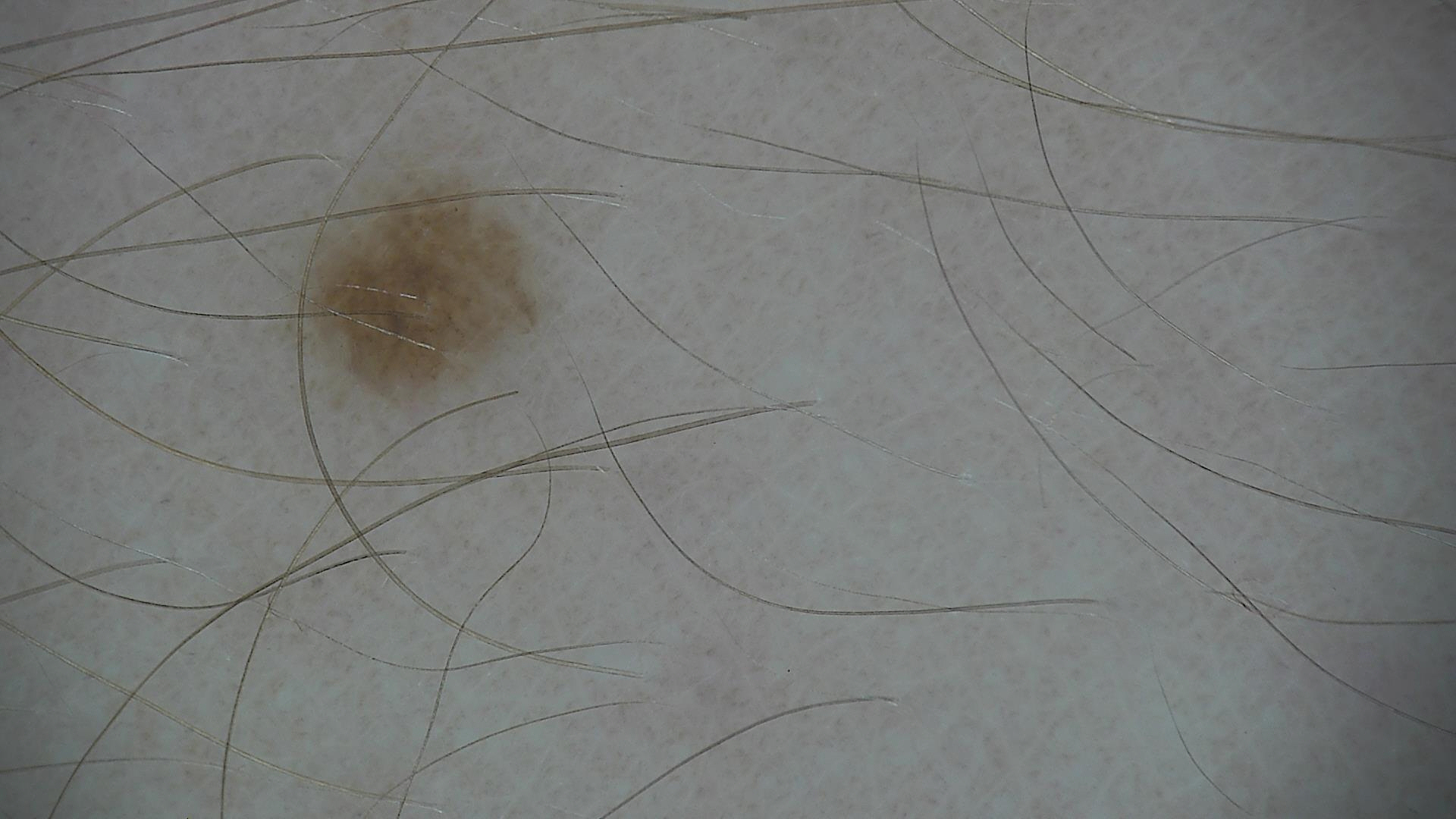A dermoscopic image of a skin lesion. Classified as a dysplastic junctional nevus.